A skin lesion imaged with a dermatoscope: 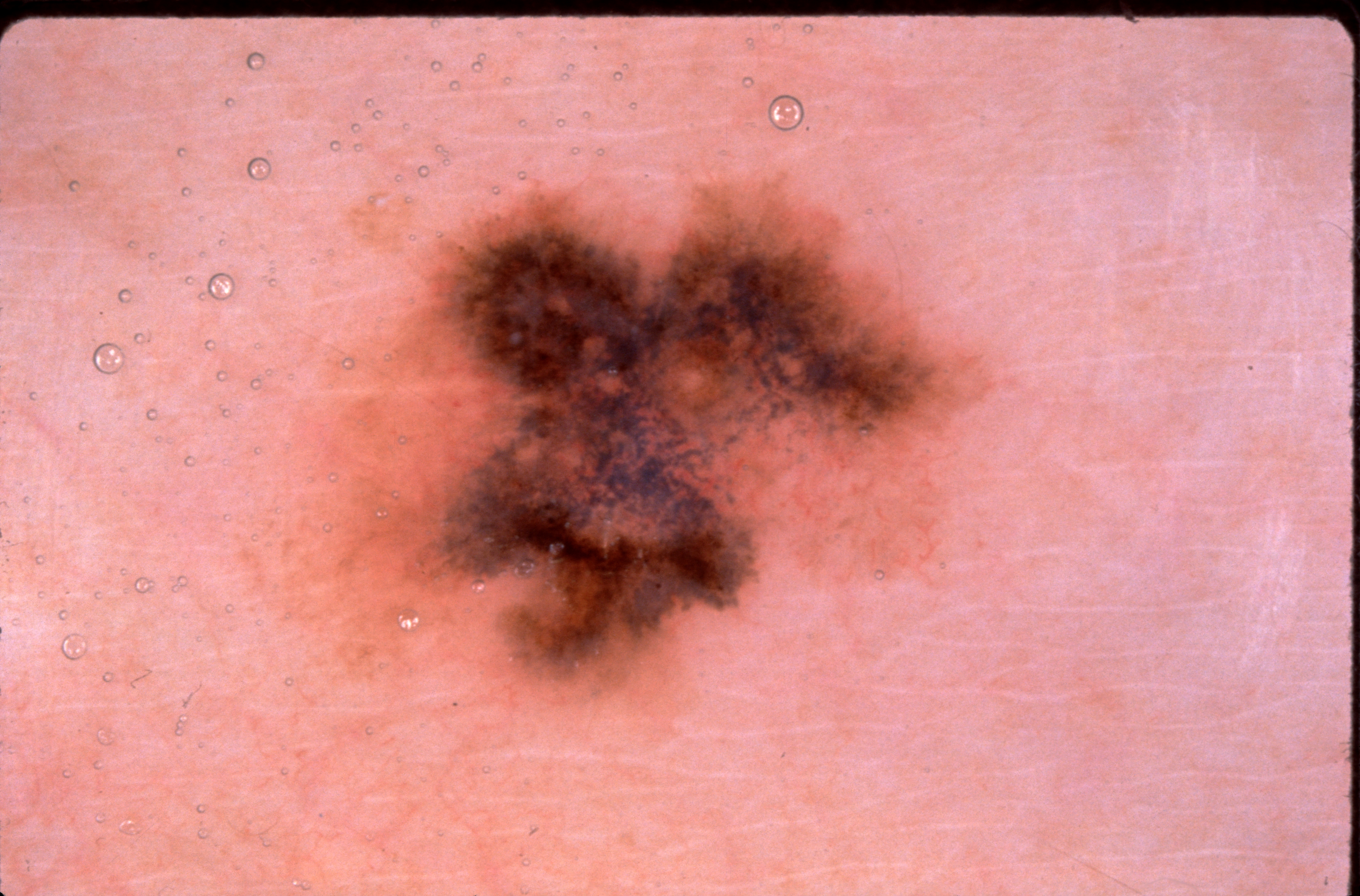| key | value |
|---|---|
| dermoscopic pattern | pigment network |
| lesion bbox | 271/126/1018/777 |
| assessment | a melanoma, a malignancy |